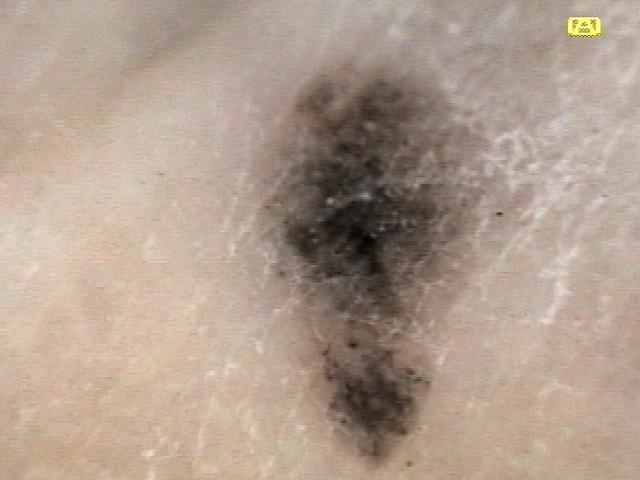A female subject in their mid-30s.
Recorded as Fitzpatrick skin type II.
A dermoscopic close-up of a skin lesion.
The lesion is on a lower extremity.
The biopsy diagnosis was a lesion of melanocytic origin — a nevus.